The photograph is a close-up of the affected area: 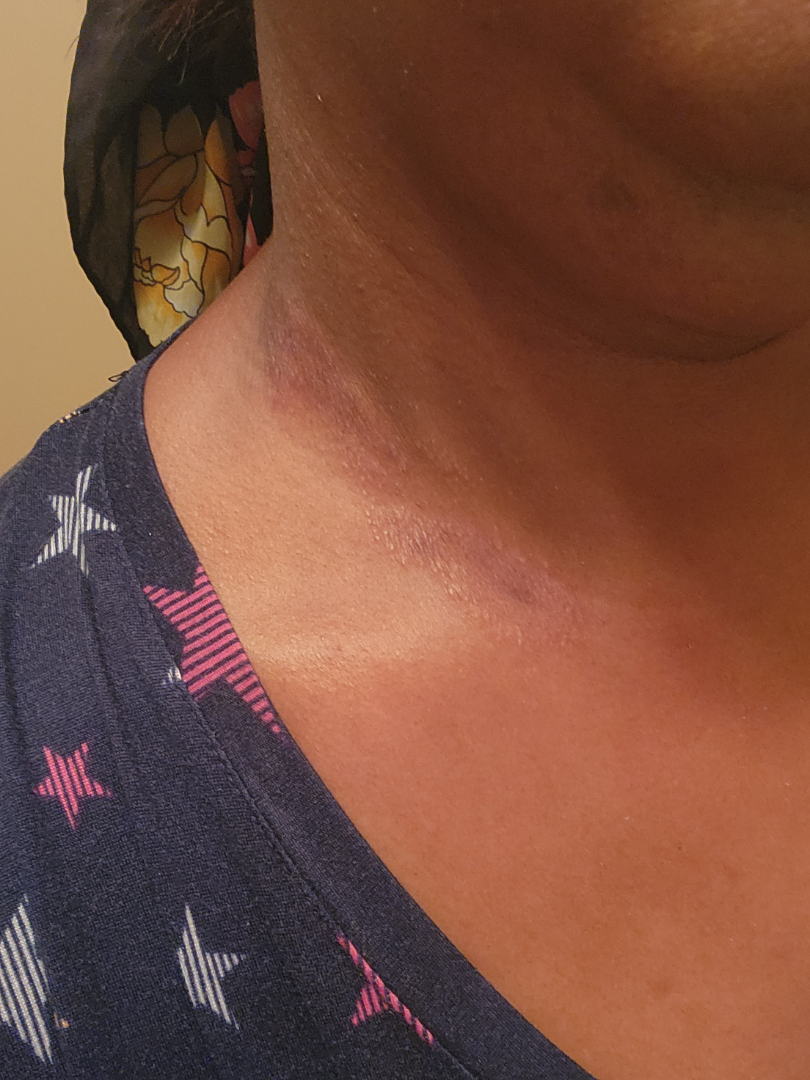Irritant Contact Dermatitis (most likely); Allergic Contact Dermatitis (possible).